The referring clinician suspected melanoma; a female patient age 50; a clinical close-up of a skin lesion: 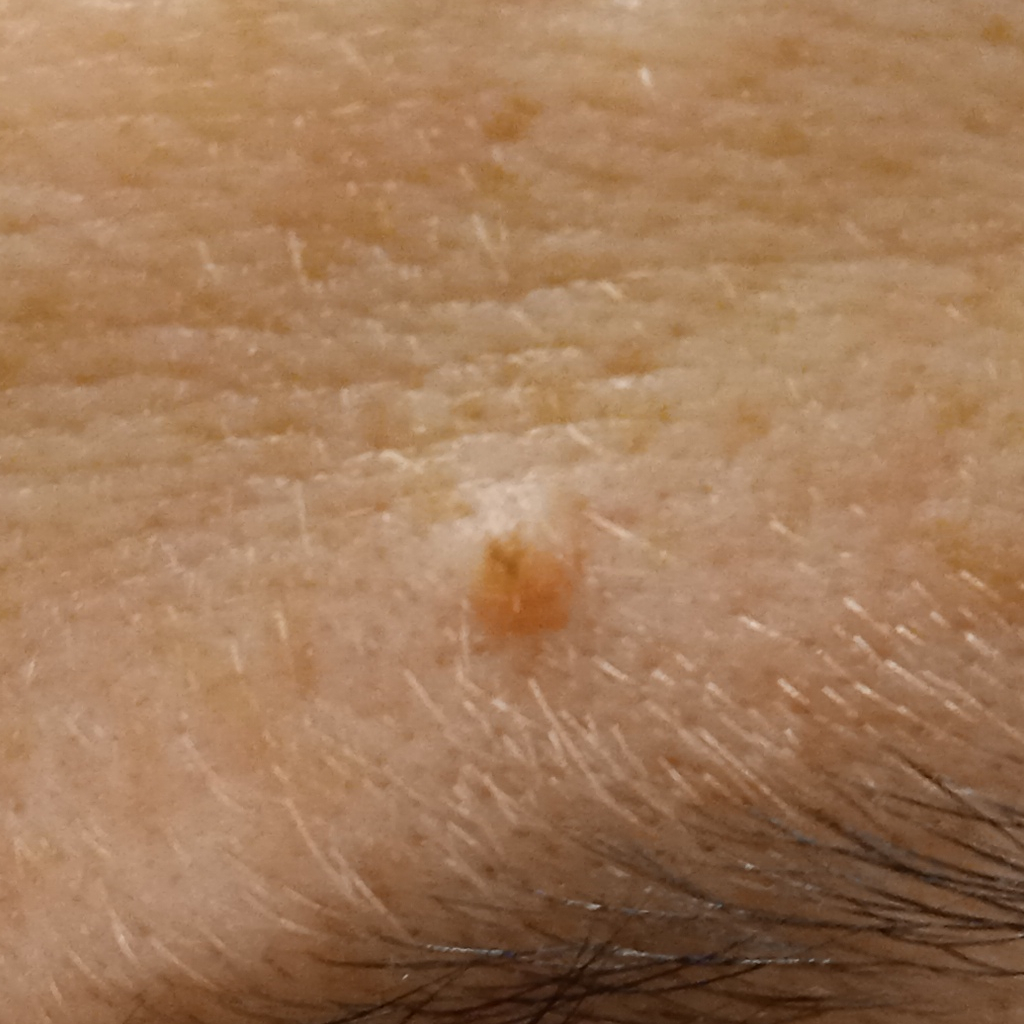  lesion_location: the face
  lesion_size:
    diameter_mm: 1.8
  diagnosis:
    name: melanocytic nevus
    malignancy: benign